The patient is a female aged 50–59; the photo was captured at an angle:
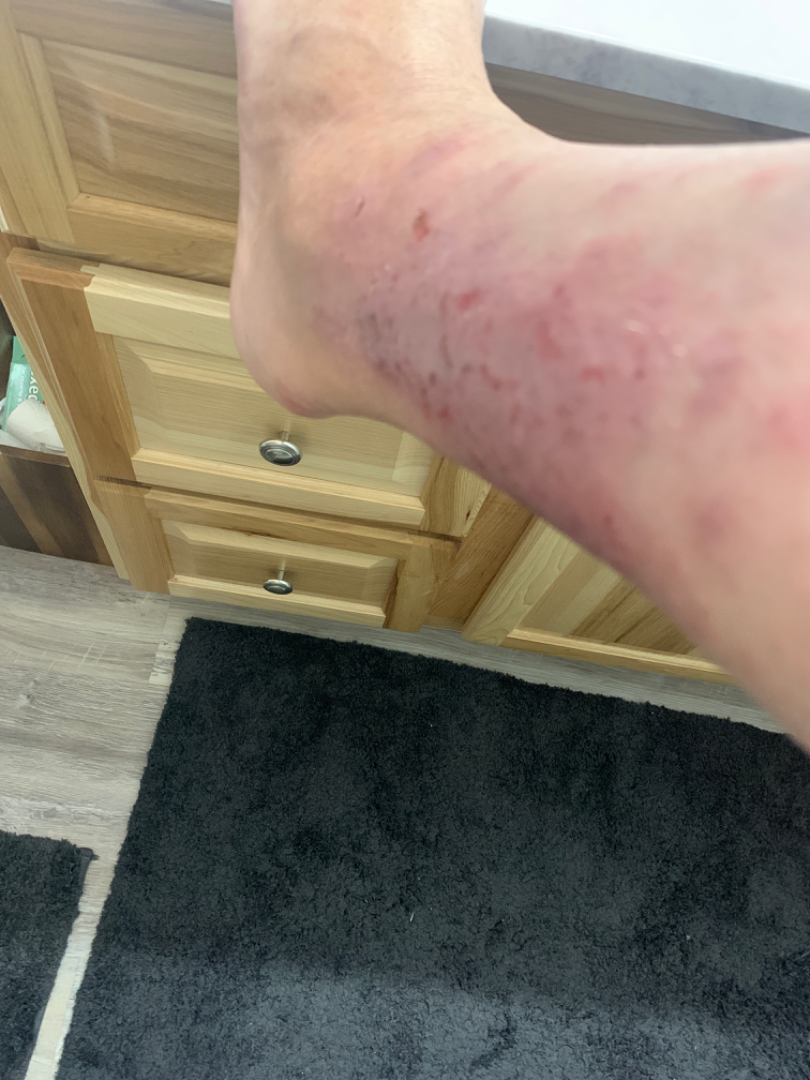Findings:
• assessment — not assessable